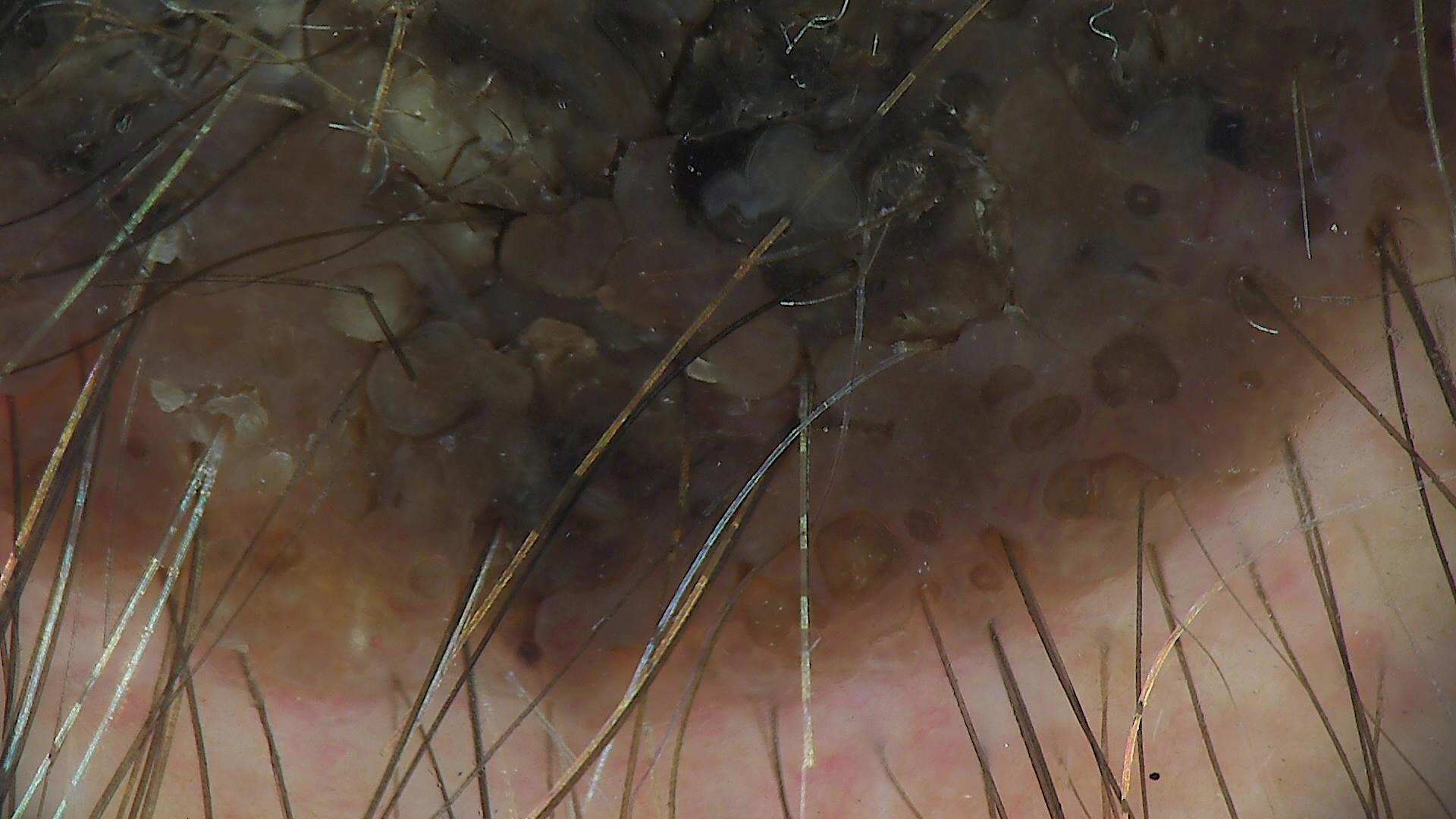Conclusion:
Classified as a congenital compound nevus.